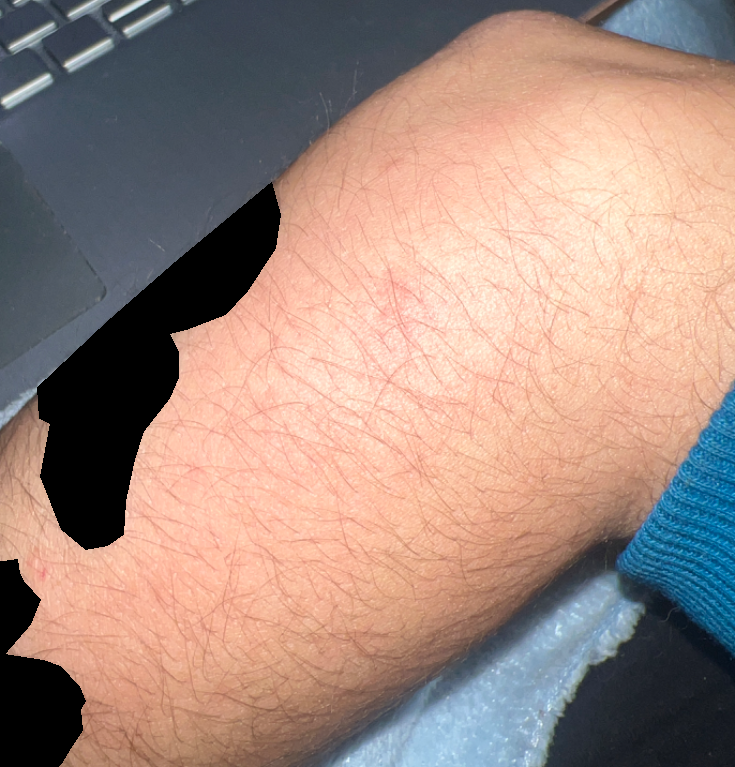Q: What was the assessment?
A: no findings on review